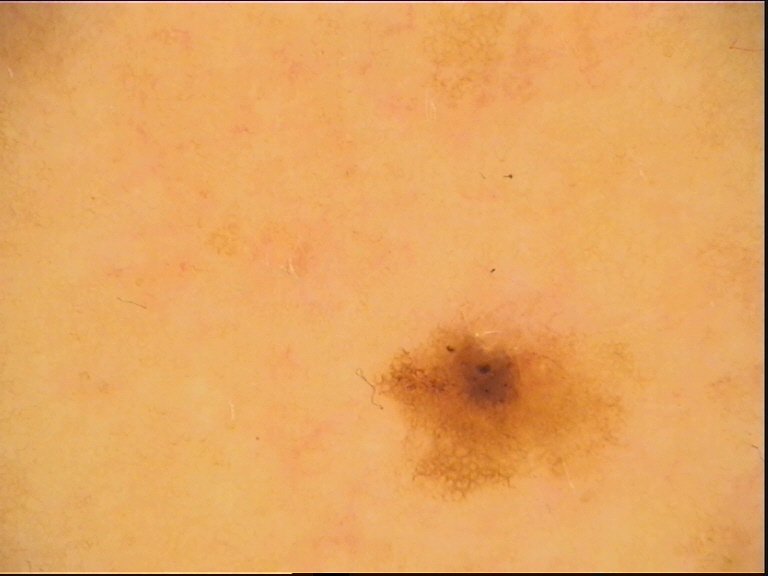diagnostic label = seborrheic keratosis (expert consensus).